A dermatoscopic image of a skin lesion.
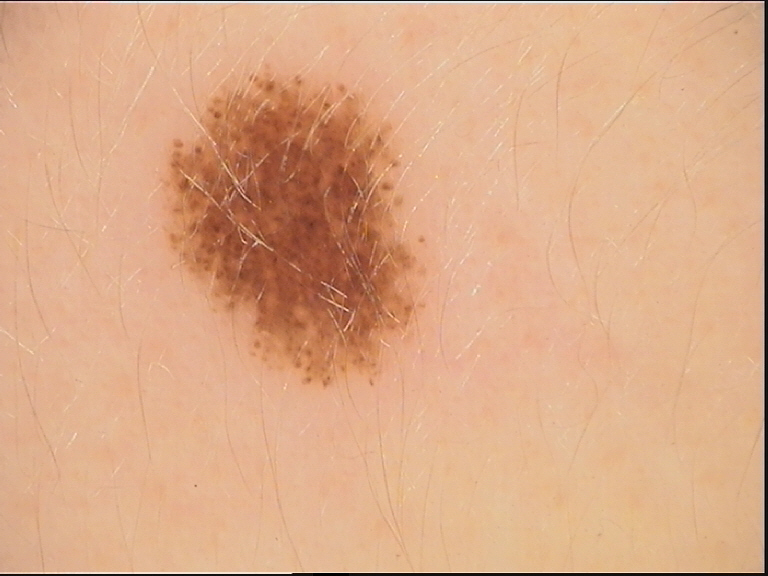Impression:
Classified as a benign lesion — a dysplastic junctional nevus.